A dermoscopic close-up of a skin lesion: 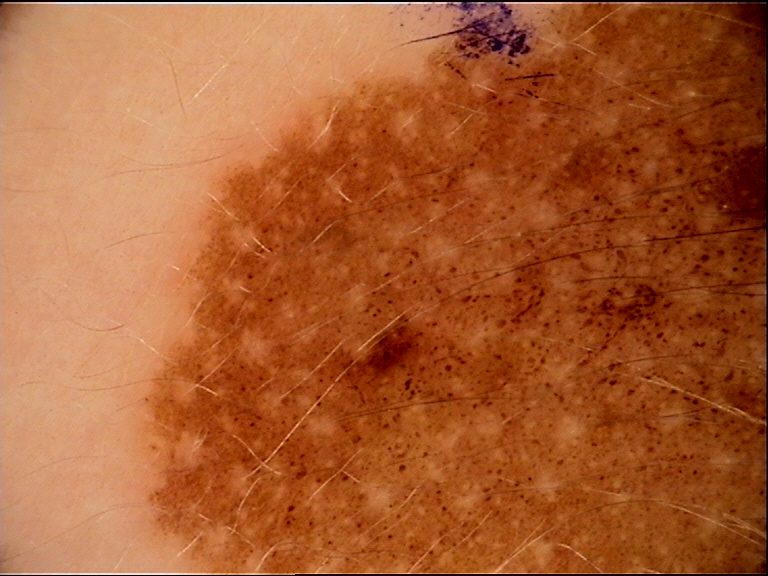Findings:
The architecture is that of a banal lesion.
Conclusion:
The diagnosis was a congenital junctional nevus.